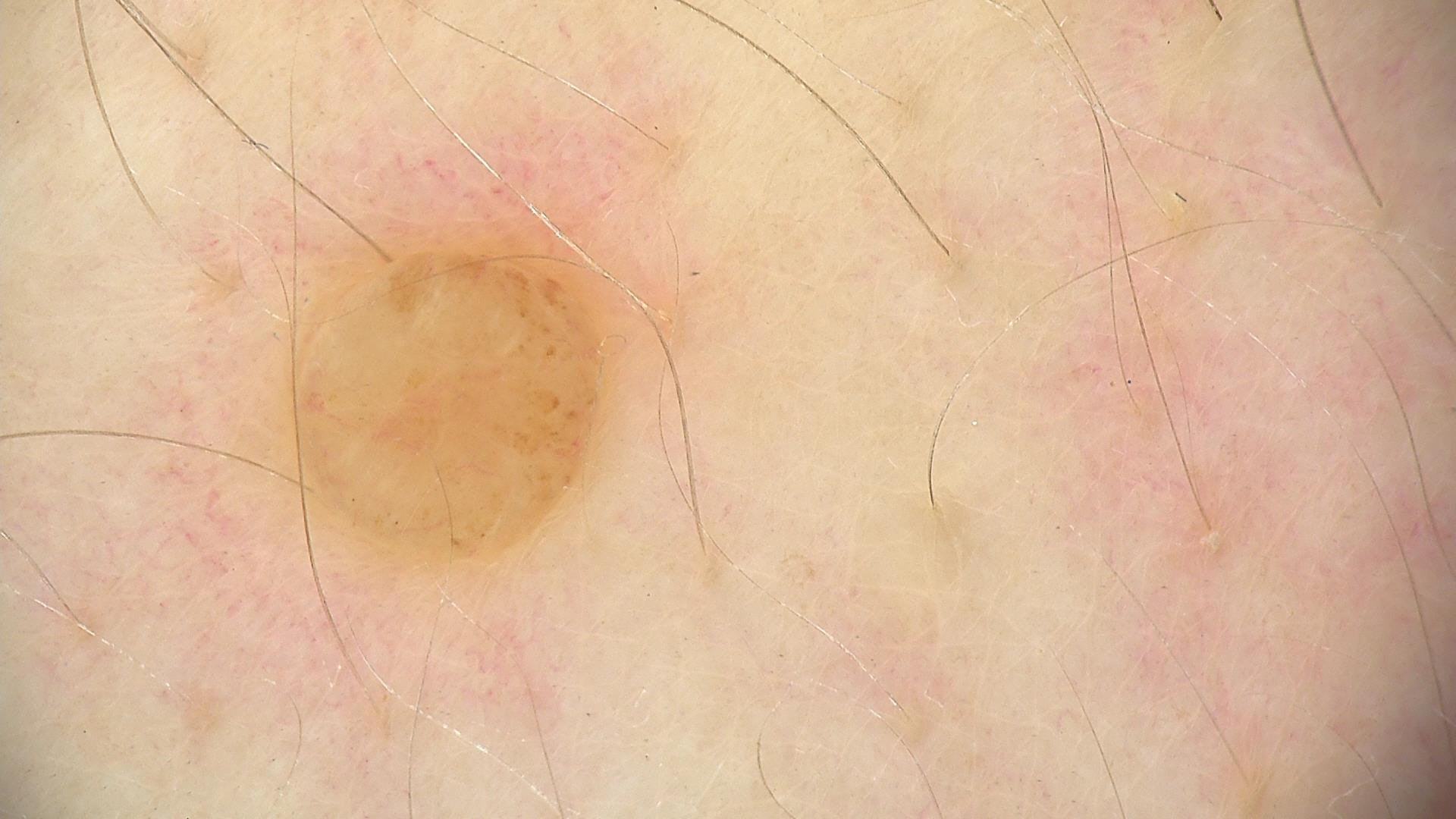image: dermoscopy | assessment: dermal nevus (expert consensus).